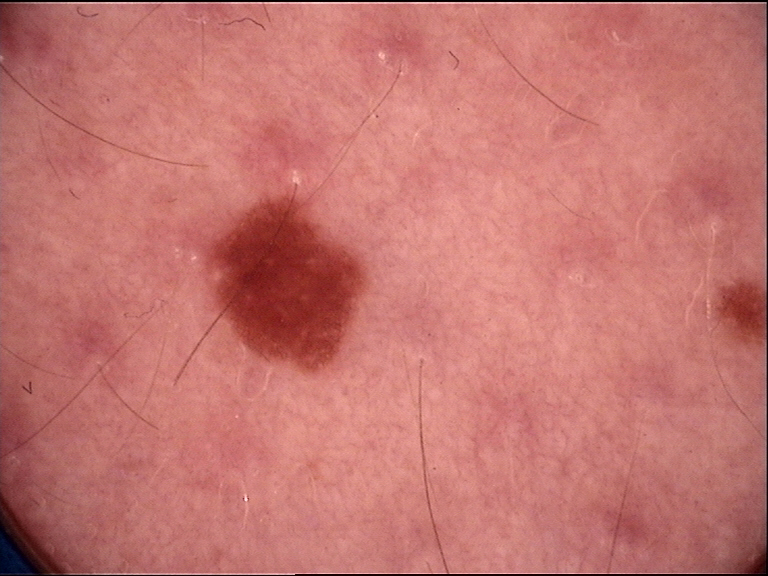modality: dermatoscopy, label: dysplastic junctional nevus (expert consensus).